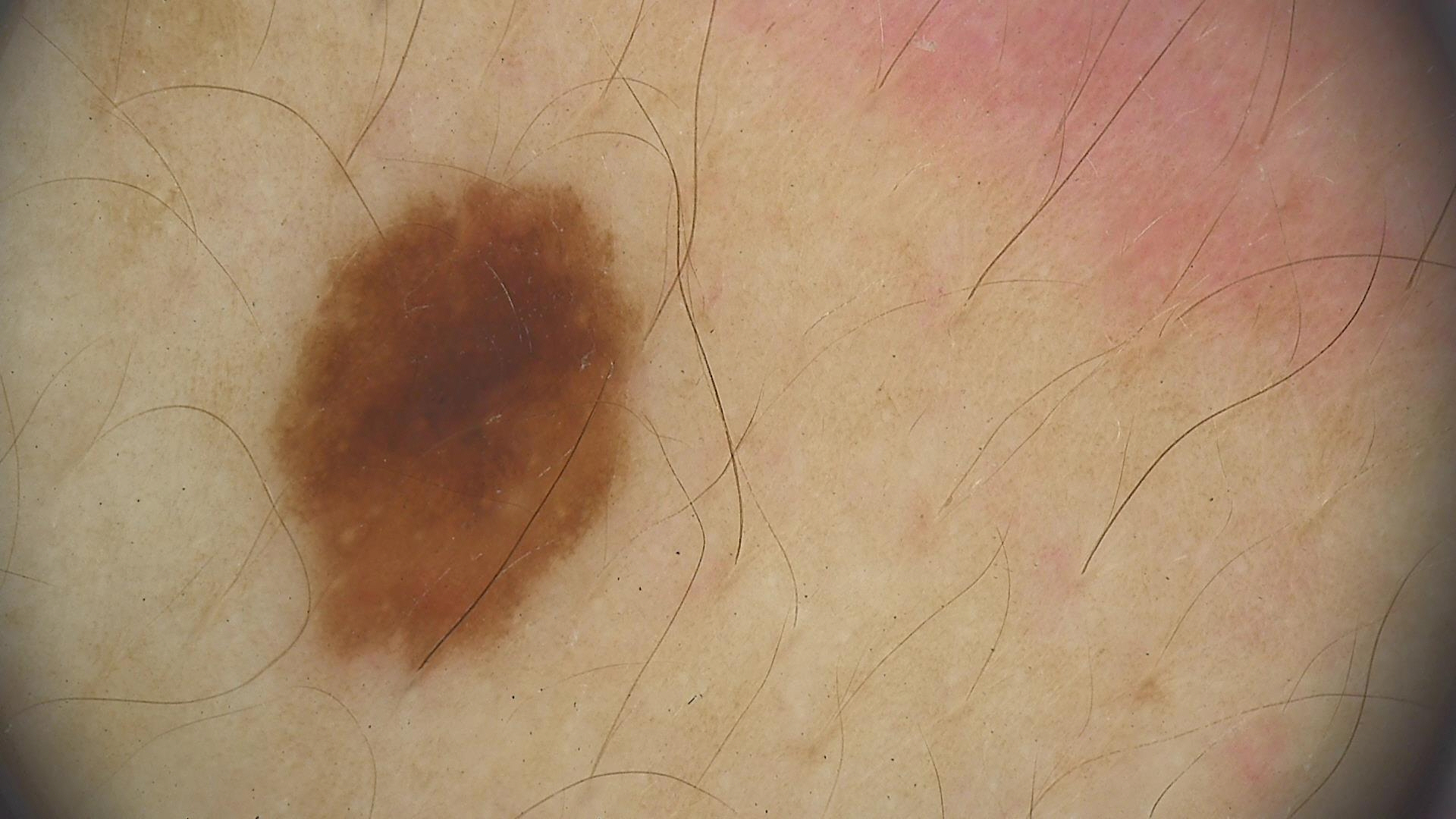diagnosis = dysplastic junctional nevus (expert consensus).